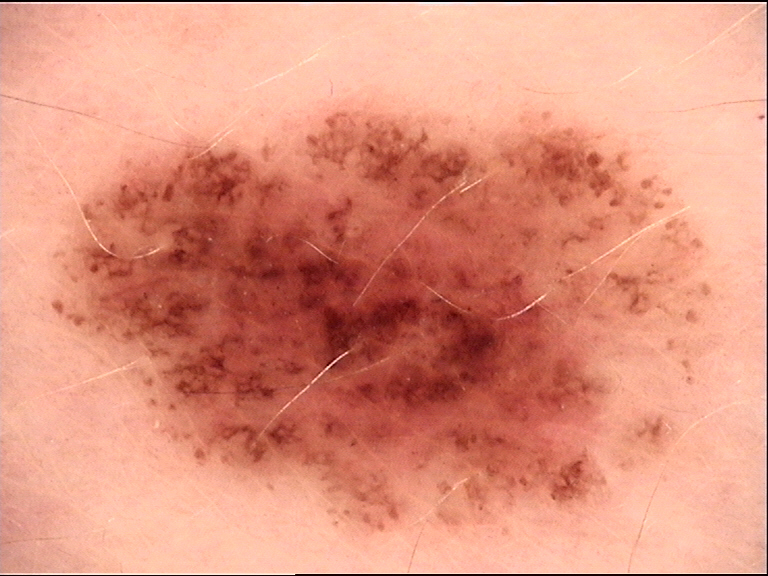Summary: A dermatoscopic image of a skin lesion. Impression: Diagnosed as a benign lesion — a dysplastic junctional nevus.